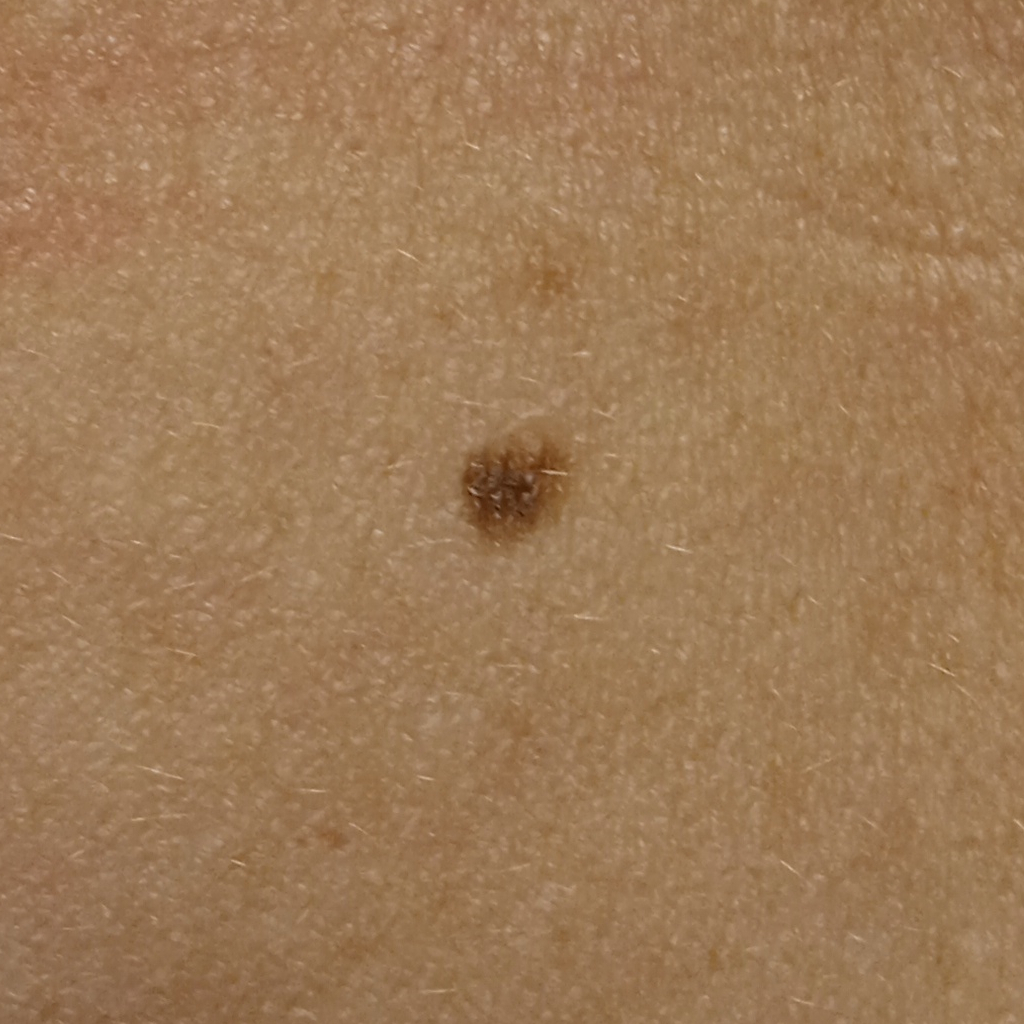<record>
<referral>research study (no referral diagnosis)</referral>
<image>clinical photograph</image>
<lesion_location>the torso</lesion_location>
<lesion_size>
<diameter_mm>5.4</diameter_mm>
</lesion_size>
<diagnosis>
<name>melanocytic nevus</name>
<malignancy>benign</malignancy>
</diagnosis>
</record>